A female subject age 75 · the patient describes having a moderate number of moles · a clinical photograph of a skin lesion · the patient reports a personal history of skin cancer and a personal history of cancer:
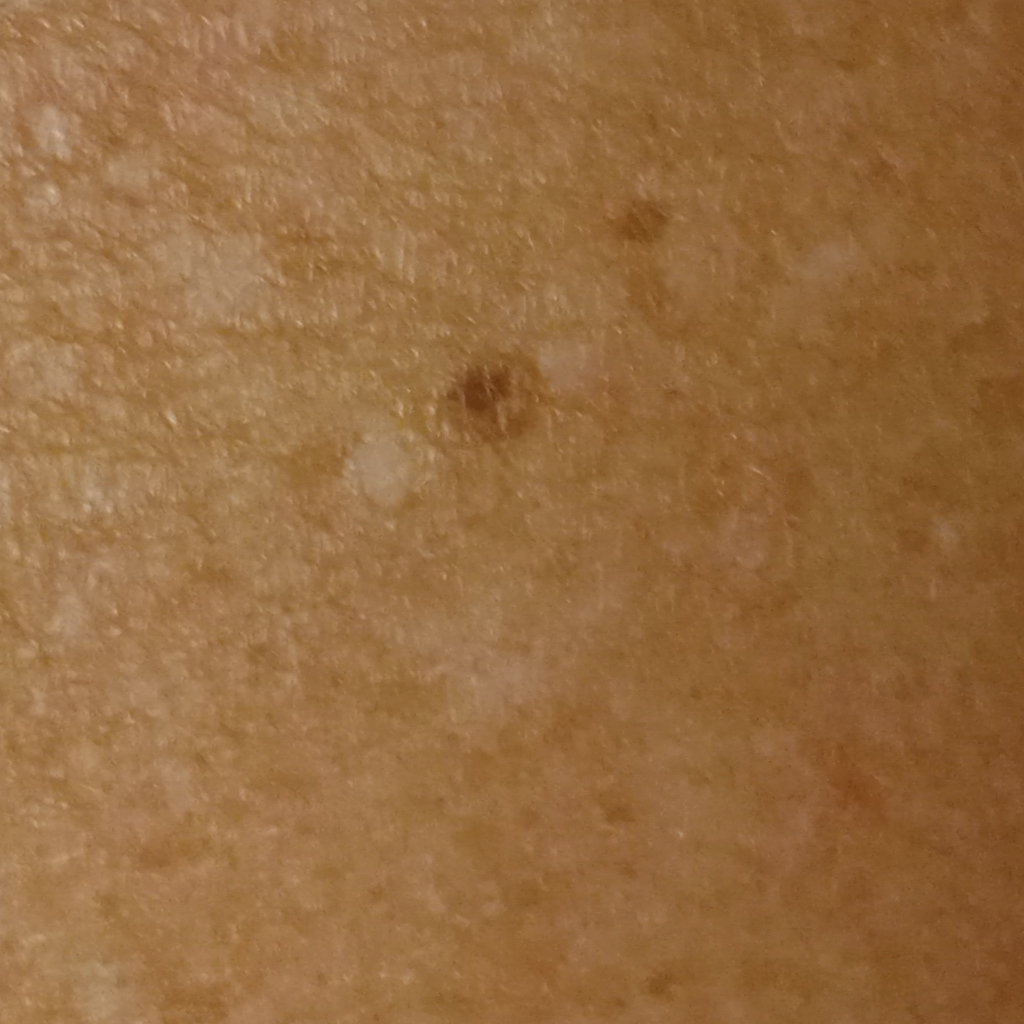  lesion_location: the back
  lesion_size:
    diameter_mm: 2.7
  diagnosis:
    name: melanocytic nevus
    malignancy: benign